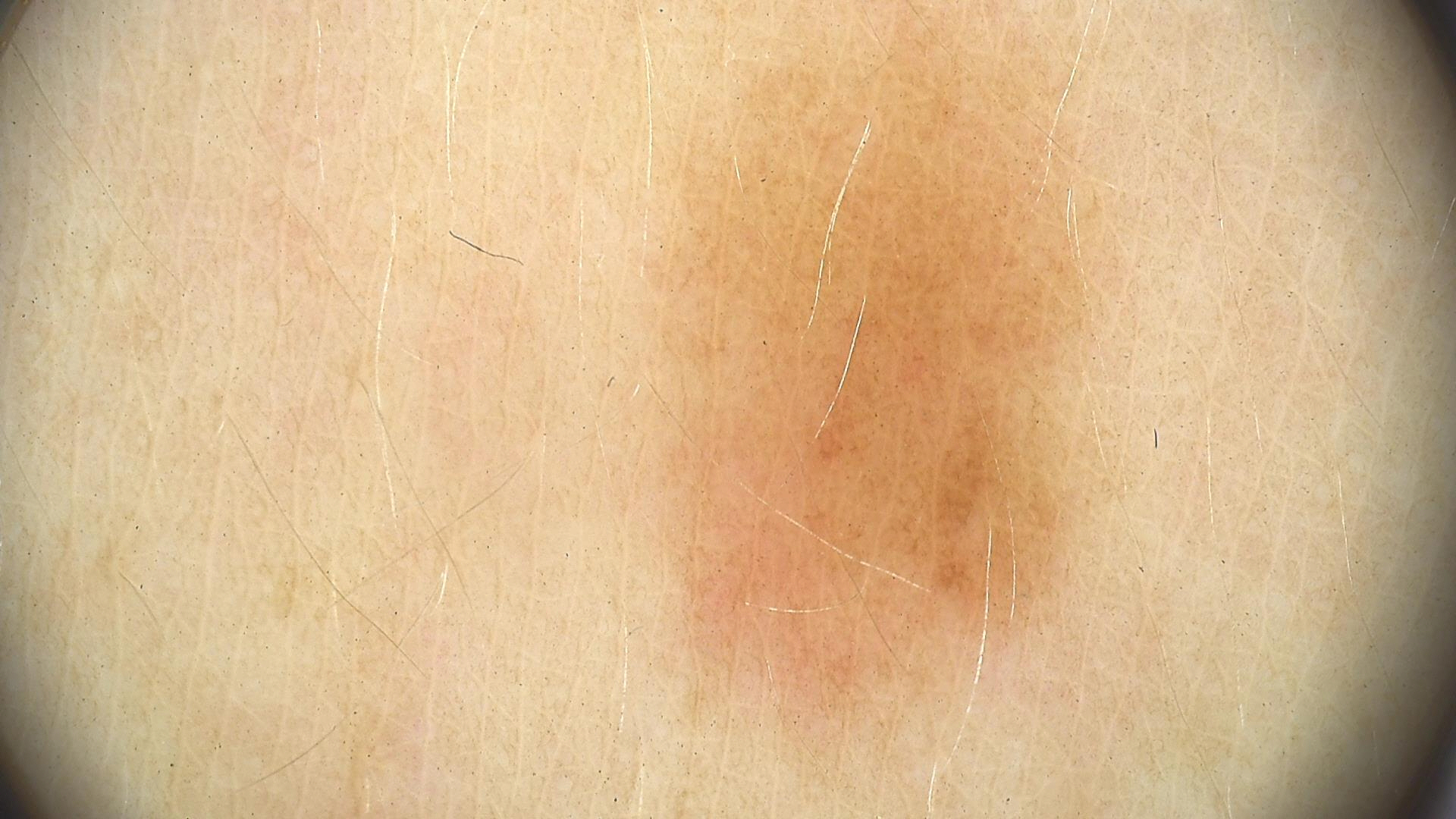A dermatoscopic image of a skin lesion. The diagnostic label was a banal lesion — a junctional nevus.